A dermatoscopic image of a skin lesion.
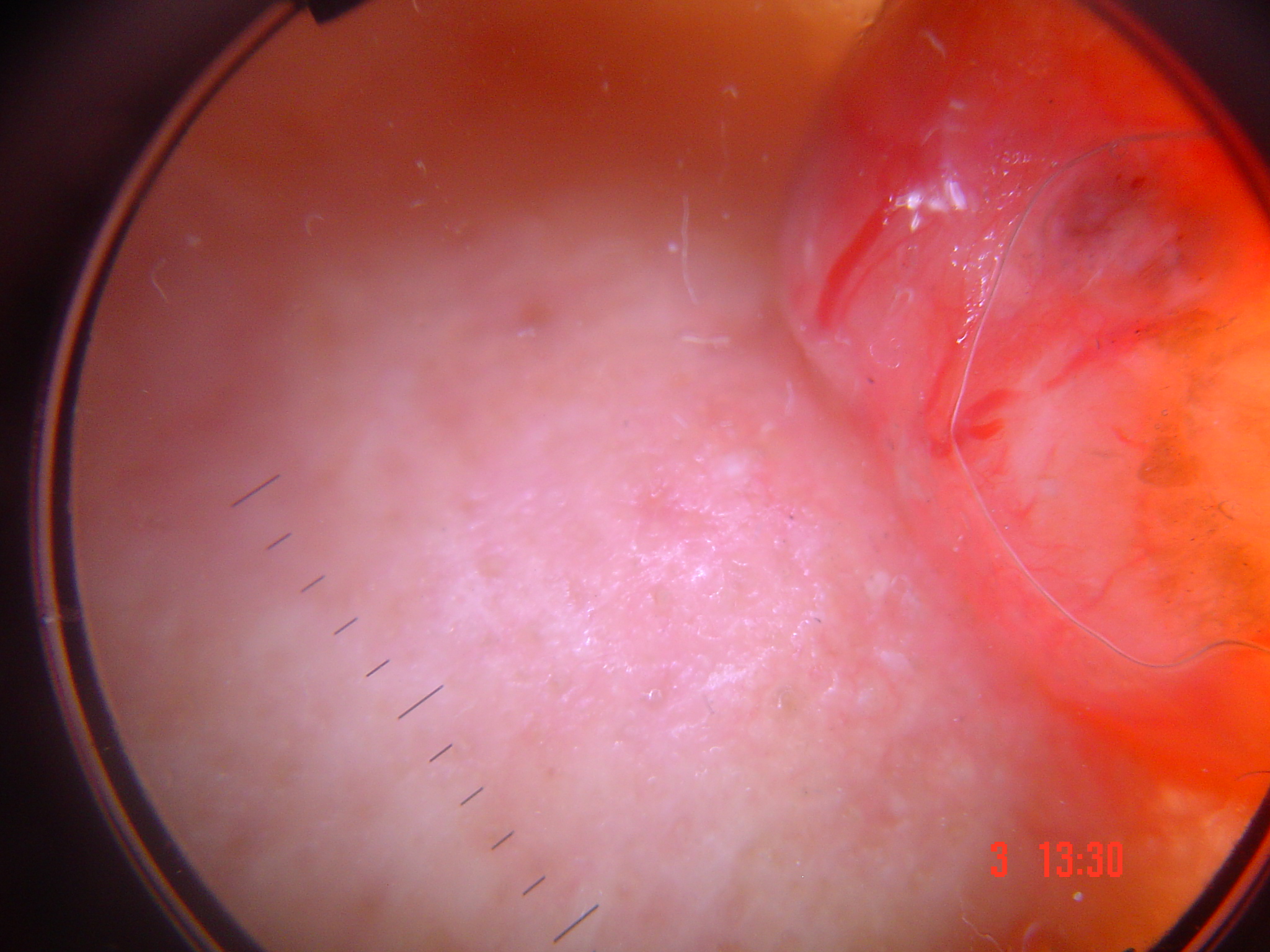diagnostic label=basal cell carcinoma (biopsy-proven)